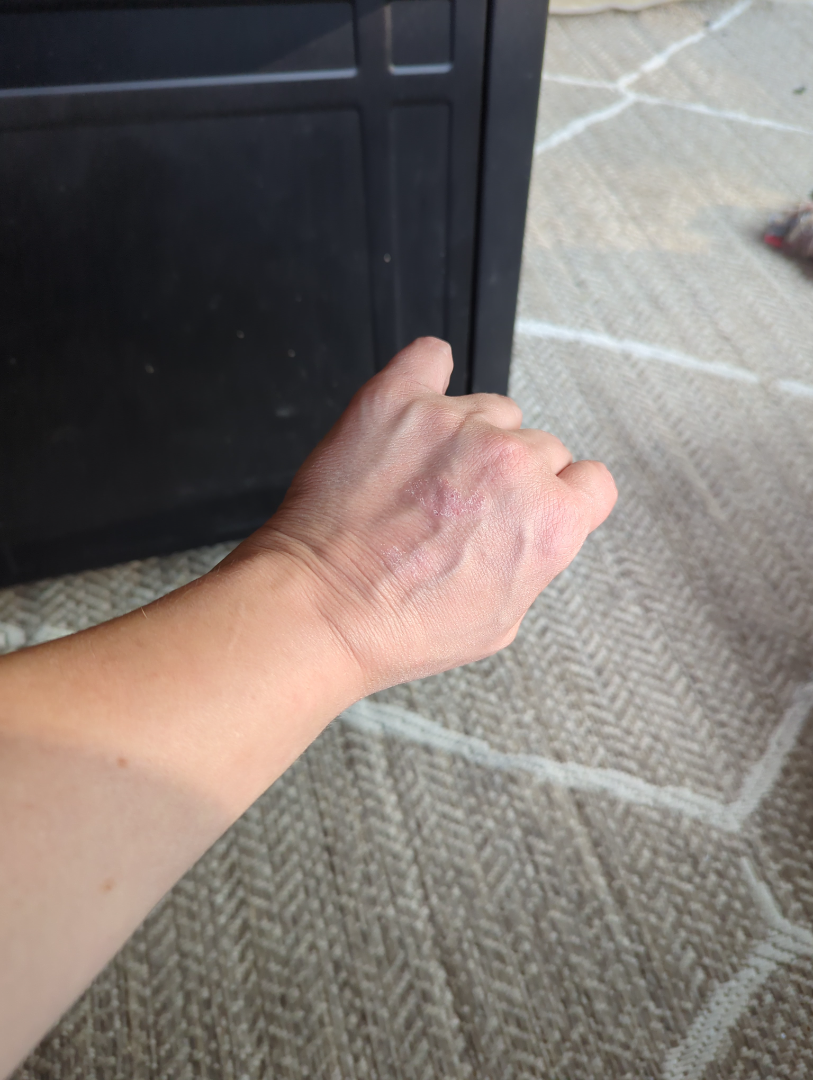Notes:
• diagnostic considerations · Psoriasis and Eczema were each considered, in no particular order; the differential also includes Contact dermatitis; less probable is Tinea